A dermatoscopic image of a skin lesion.
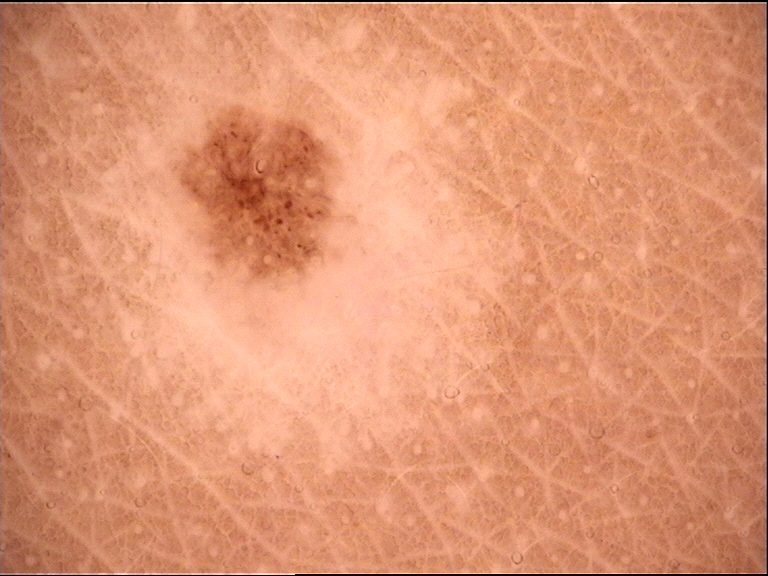diagnosis: dysplastic junctional nevus (expert consensus)